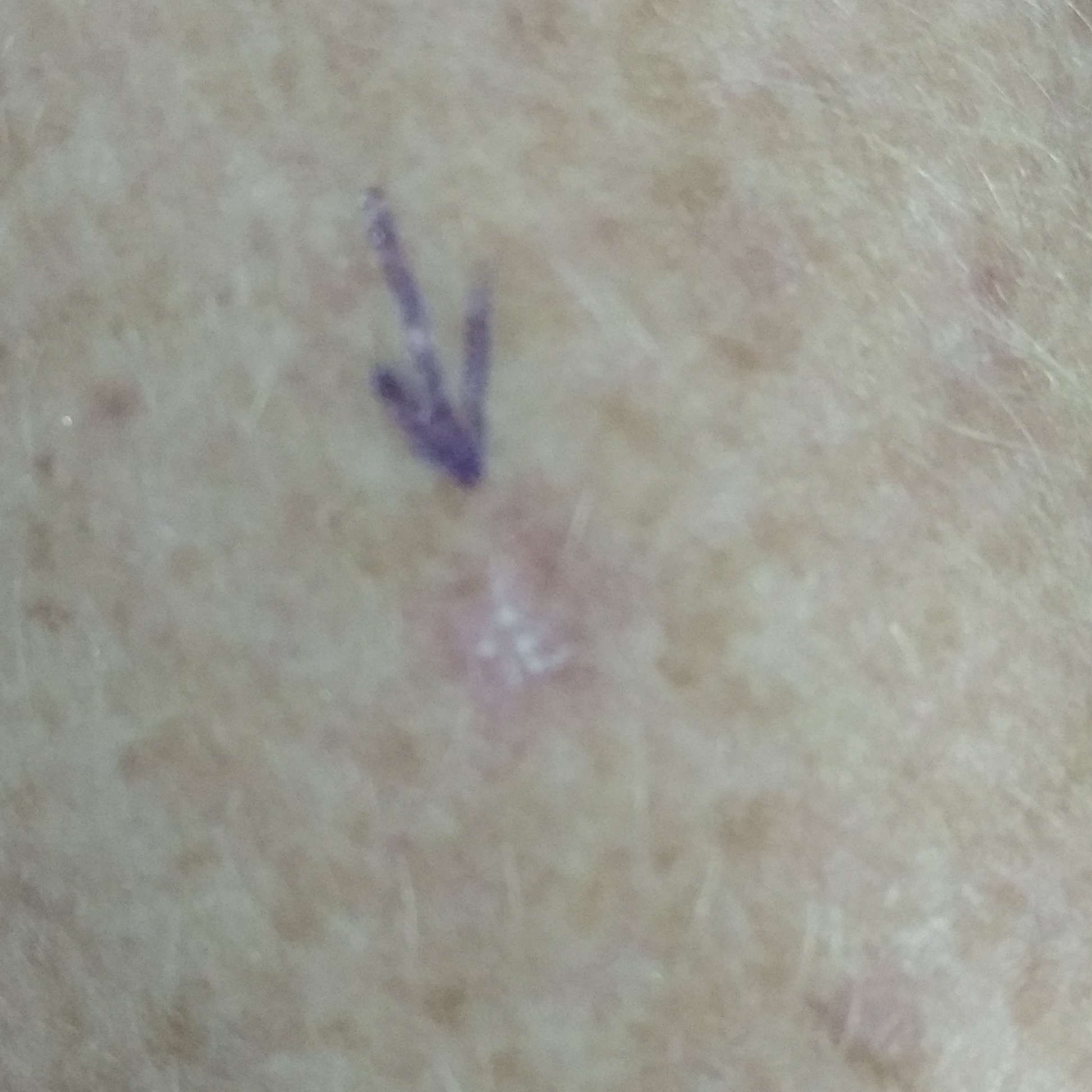{"skin_type": "II", "patient": {"age": 52, "gender": "female"}, "symptoms": {"present": ["itching"], "absent": ["change in appearance"]}, "diagnosis": {"name": "actinic keratosis", "code": "ACK", "malignancy": "indeterminate", "confirmation": "clinical consensus"}}